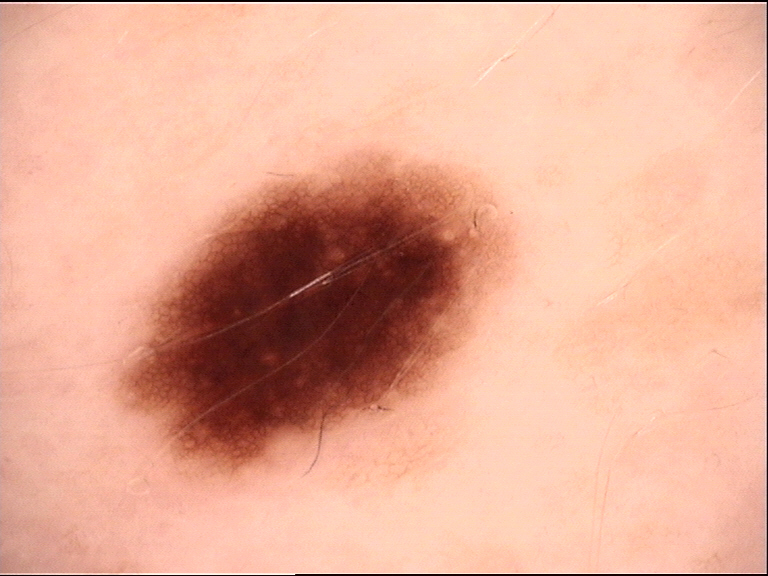Labeled as a dysplastic junctional nevus.